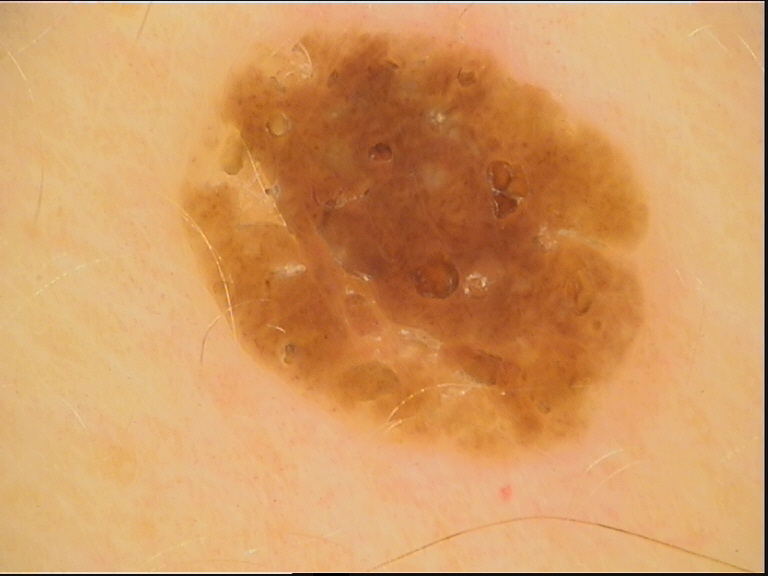A dermoscopy image of a single skin lesion.
The morphology is that of a keratinocytic lesion.
The diagnostic label was a seborrheic keratosis.